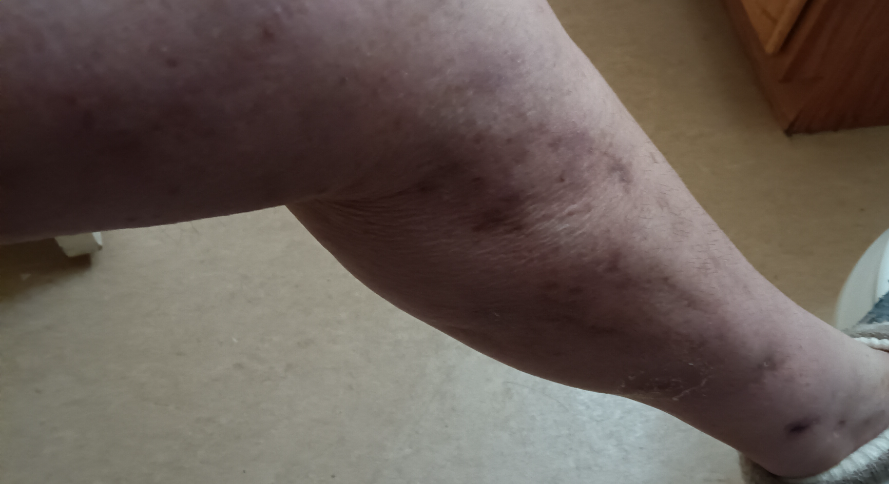The image was not sufficient for the reviewer to characterize the skin condition.
The photo was captured at an angle.
The arm and leg are involved.
Reported duration is three to twelve months.
Symptoms reported: bothersome appearance and enlargement.
Skin tone: lay reviewers estimated MST 5 or 6 (two reviewer pools).